A male patient aged around 25. A dermoscopy image of a single skin lesion.
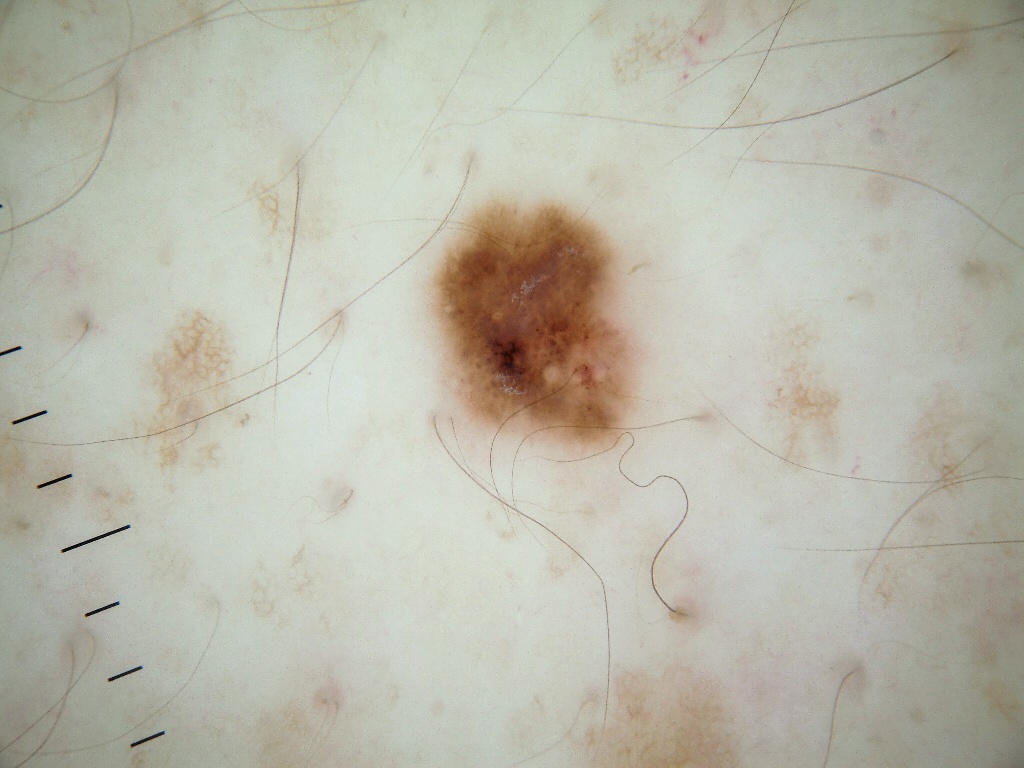lesion location = box(428, 195, 642, 456)
features = negative network and pigment network; absent: globules, milia-like cysts, and streaks
diagnosis = a melanocytic nevus, a benign lesion